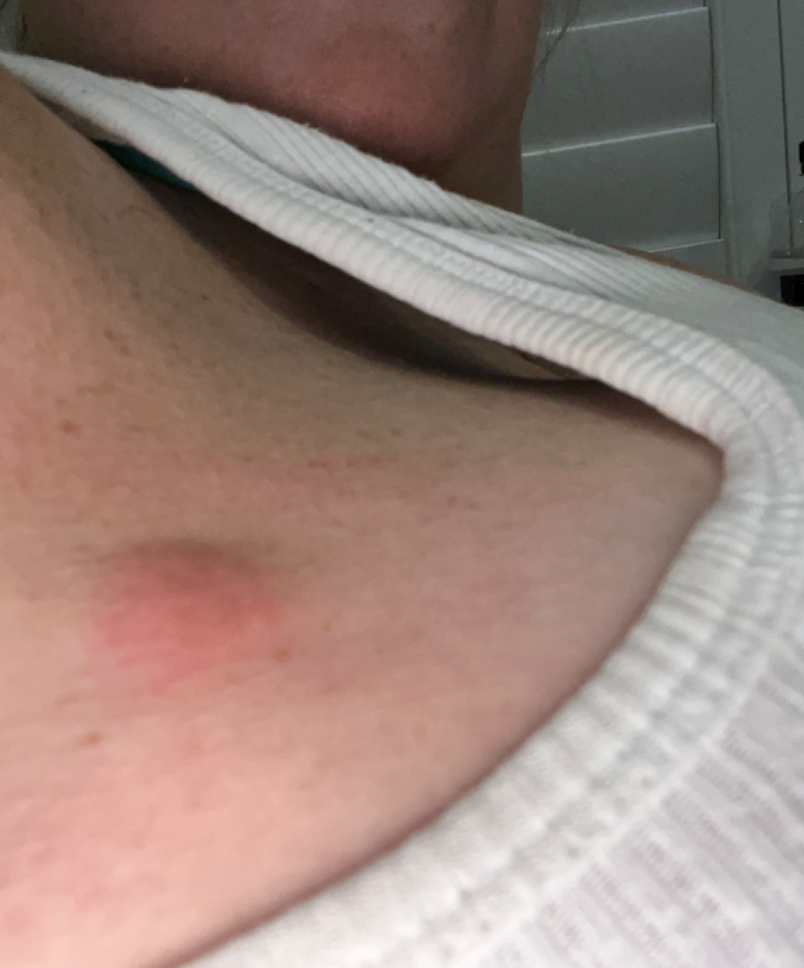skin tone = Fitzpatrick phototype II; lay reviewers estimated 2 on the Monk skin tone scale | framing = close-up | associated systemic symptoms = fatigue | anatomic site = arm | contributor = female, age 50–59 | patient-reported symptoms = bothersome appearance and itching | self-categorized as = a rash | present for = less than one week | texture = raised or bumpy | differential diagnosis = most consistent with Abscess.